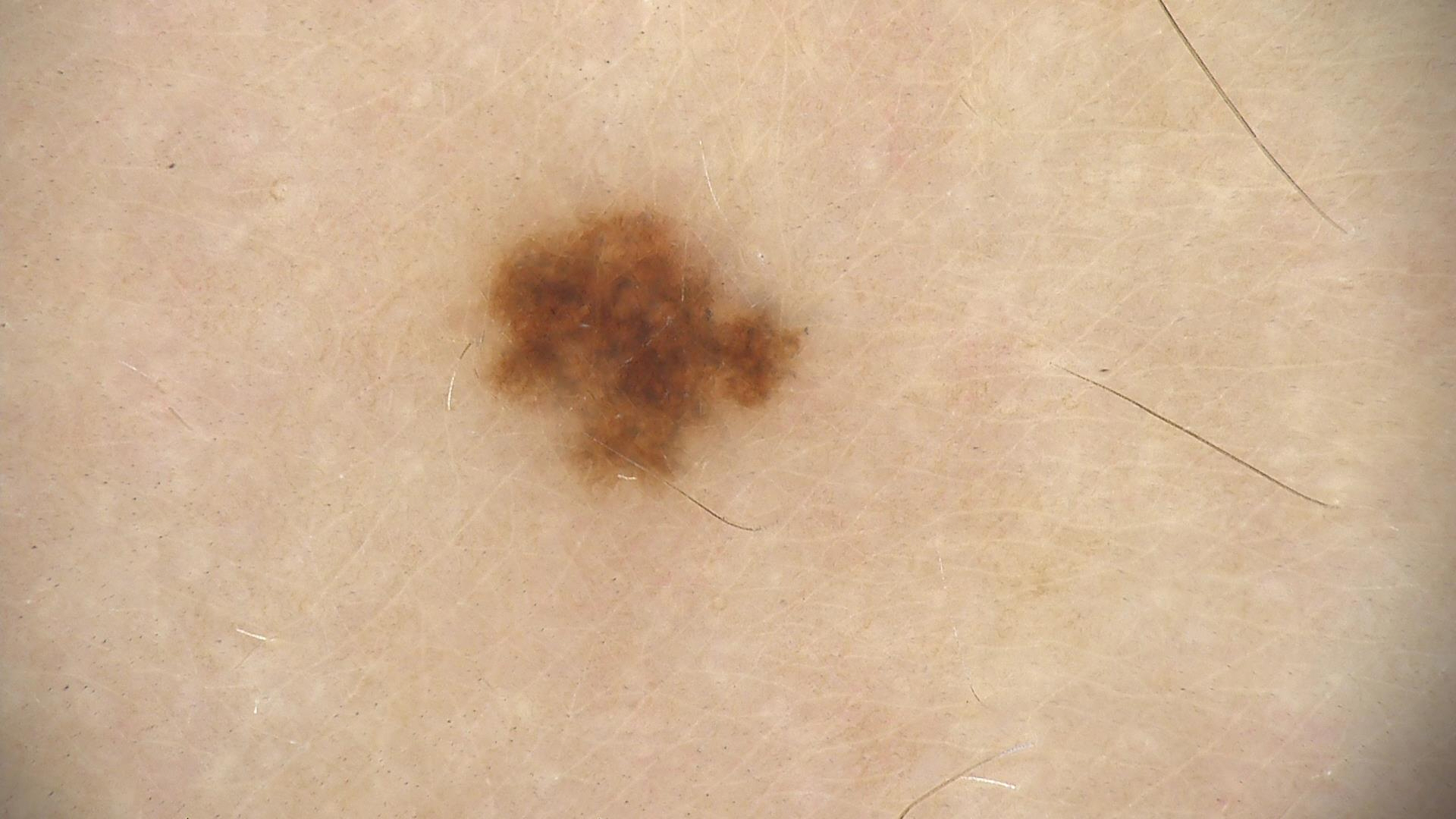diagnostic label — dysplastic junctional nevus (expert consensus).